A dermoscopic image of a skin lesion:
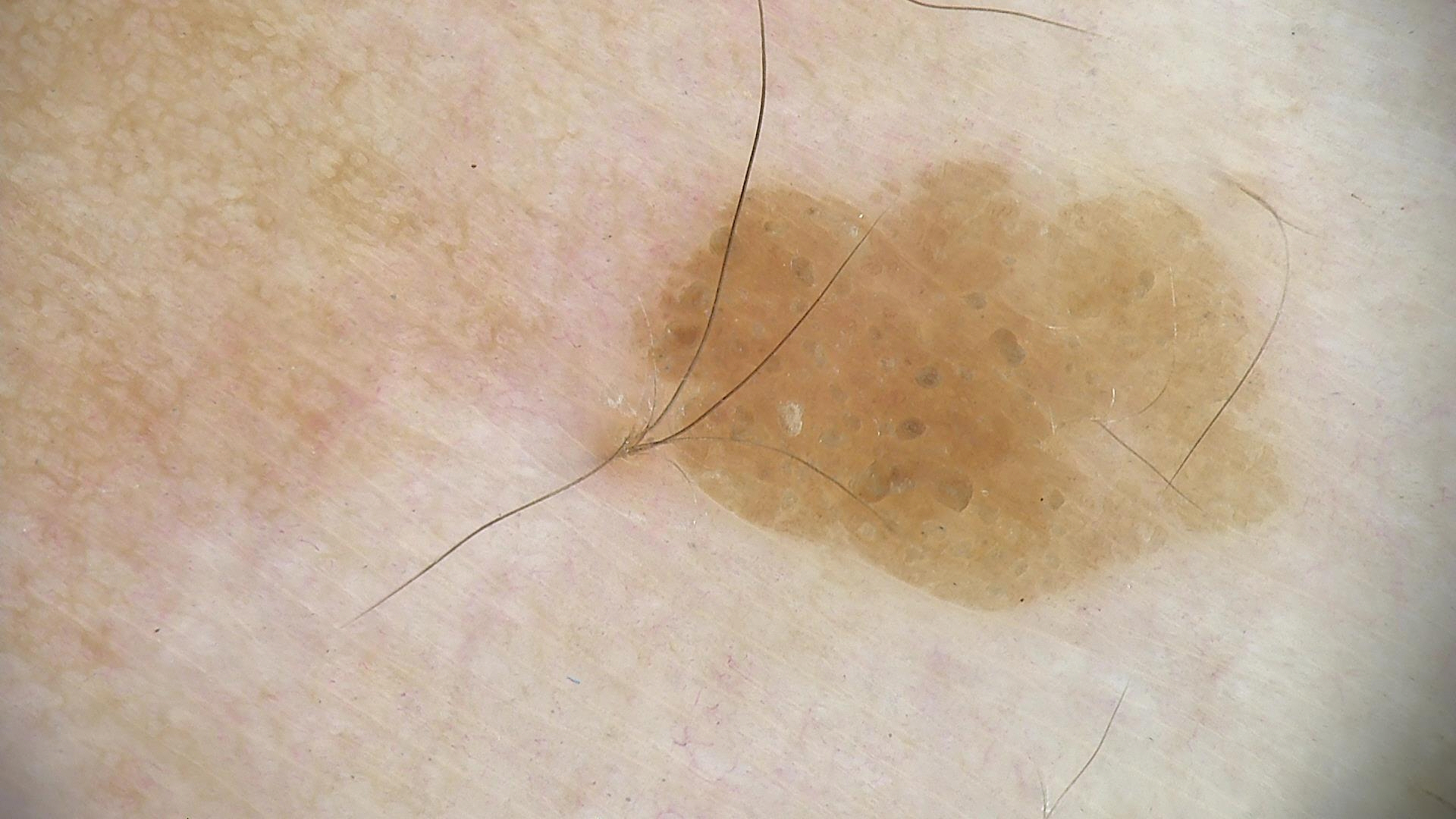| field | value |
|---|---|
| classification | keratinocytic |
| diagnostic label | seborrheic keratosis (expert consensus) |